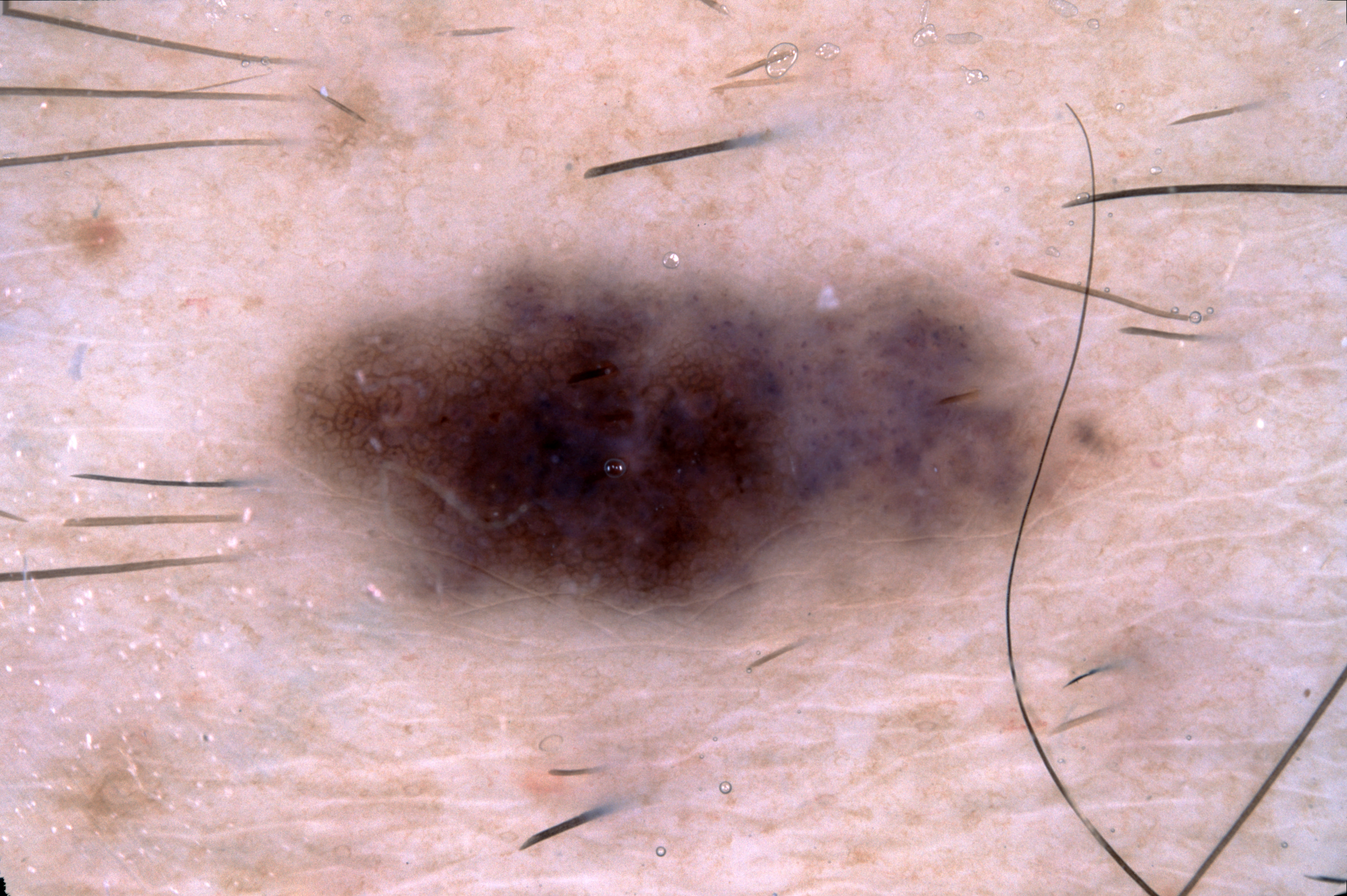A male patient, aged around 50.
A dermoscopic image of a skin lesion.
The lesion takes up a moderate portion of the field.
Dermoscopic review identifies pigment network.
With coordinates (x1, y1, x2, y2), lesion location: <bbox>249, 203, 1145, 665</bbox>.
Consistent with a melanocytic nevus.